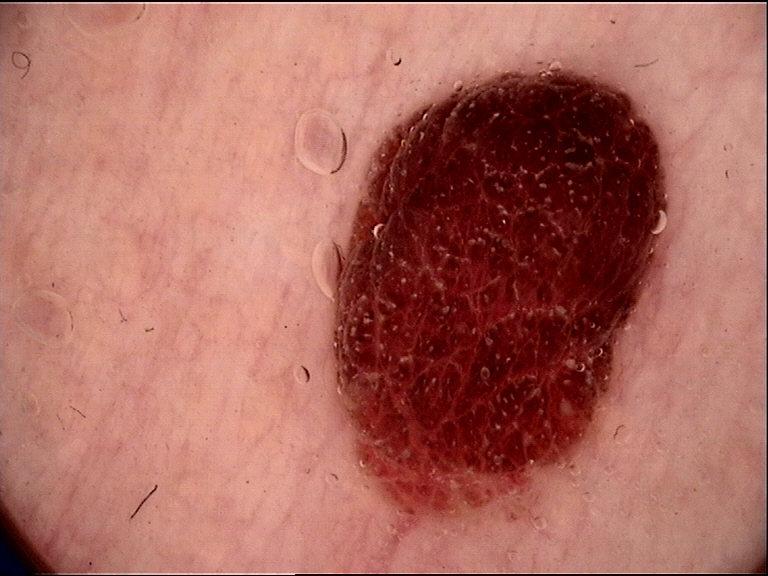<lesion>
  <diagnosis>
    <name>compound nevus</name>
    <code>cb</code>
    <malignancy>benign</malignancy>
    <super_class>melanocytic</super_class>
    <confirmation>expert consensus</confirmation>
  </diagnosis>
</lesion>